A dermoscopy image of a single skin lesion:
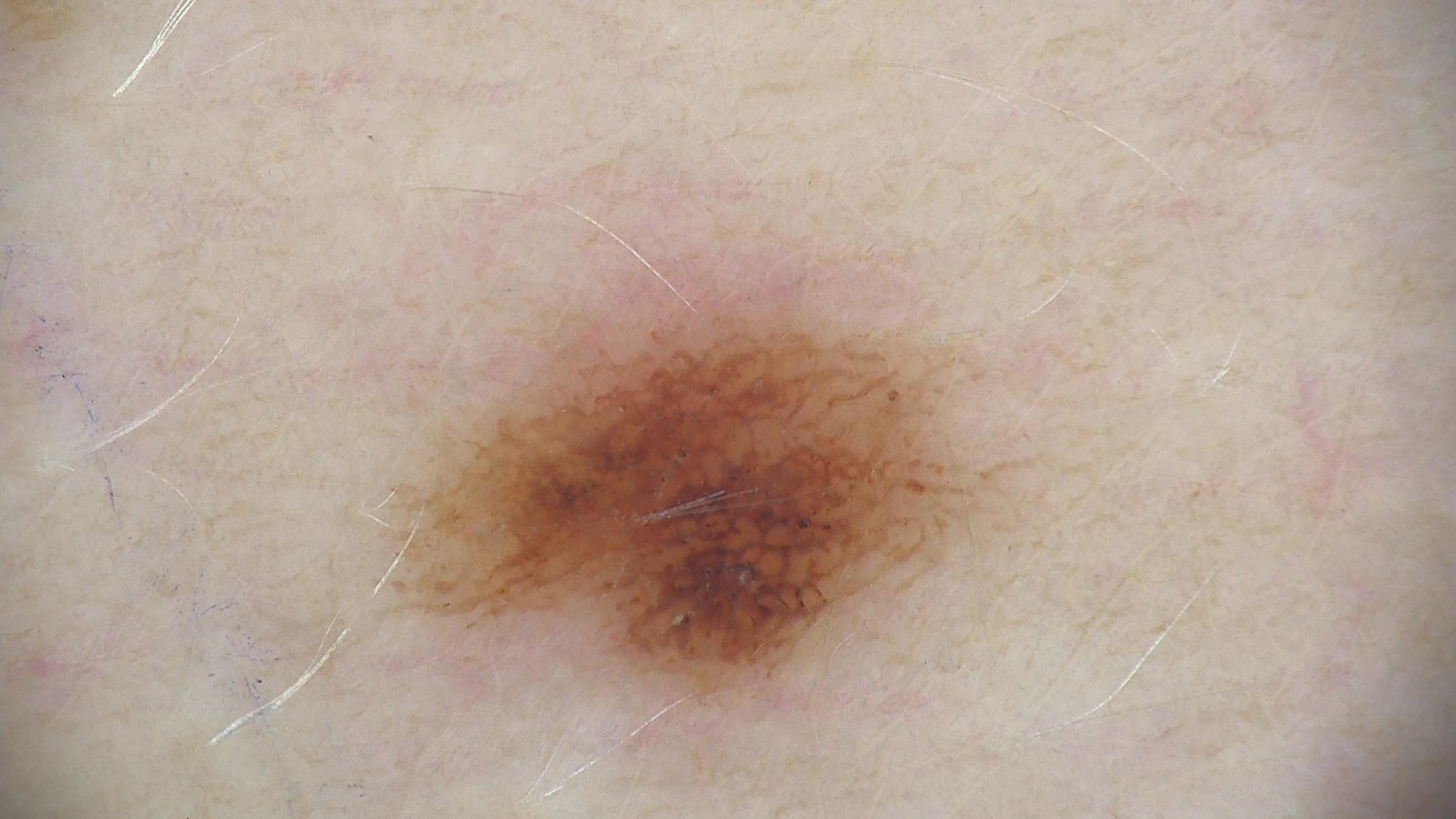- assessment · dysplastic junctional nevus (expert consensus)